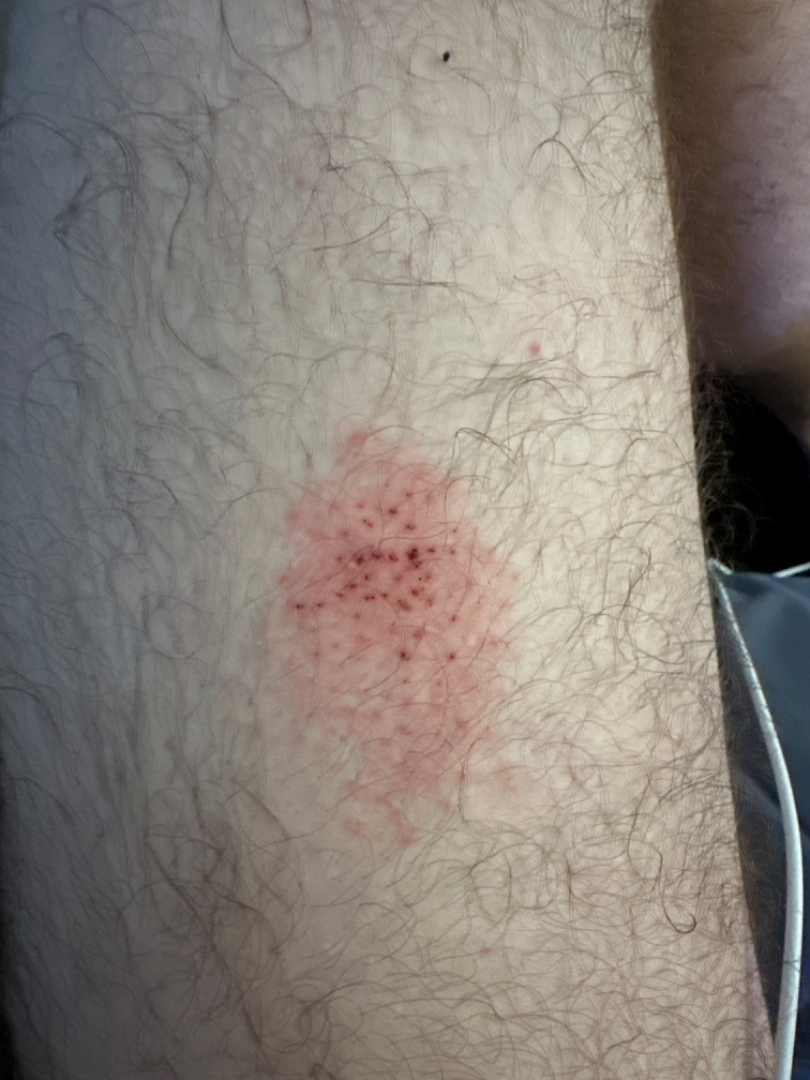patient = male, age 30–39
photo taken = close-up
duration = less than one week
anatomic site = leg
differential = the favored diagnosis is Abrasion, scrape, or scab; possibly Eczema